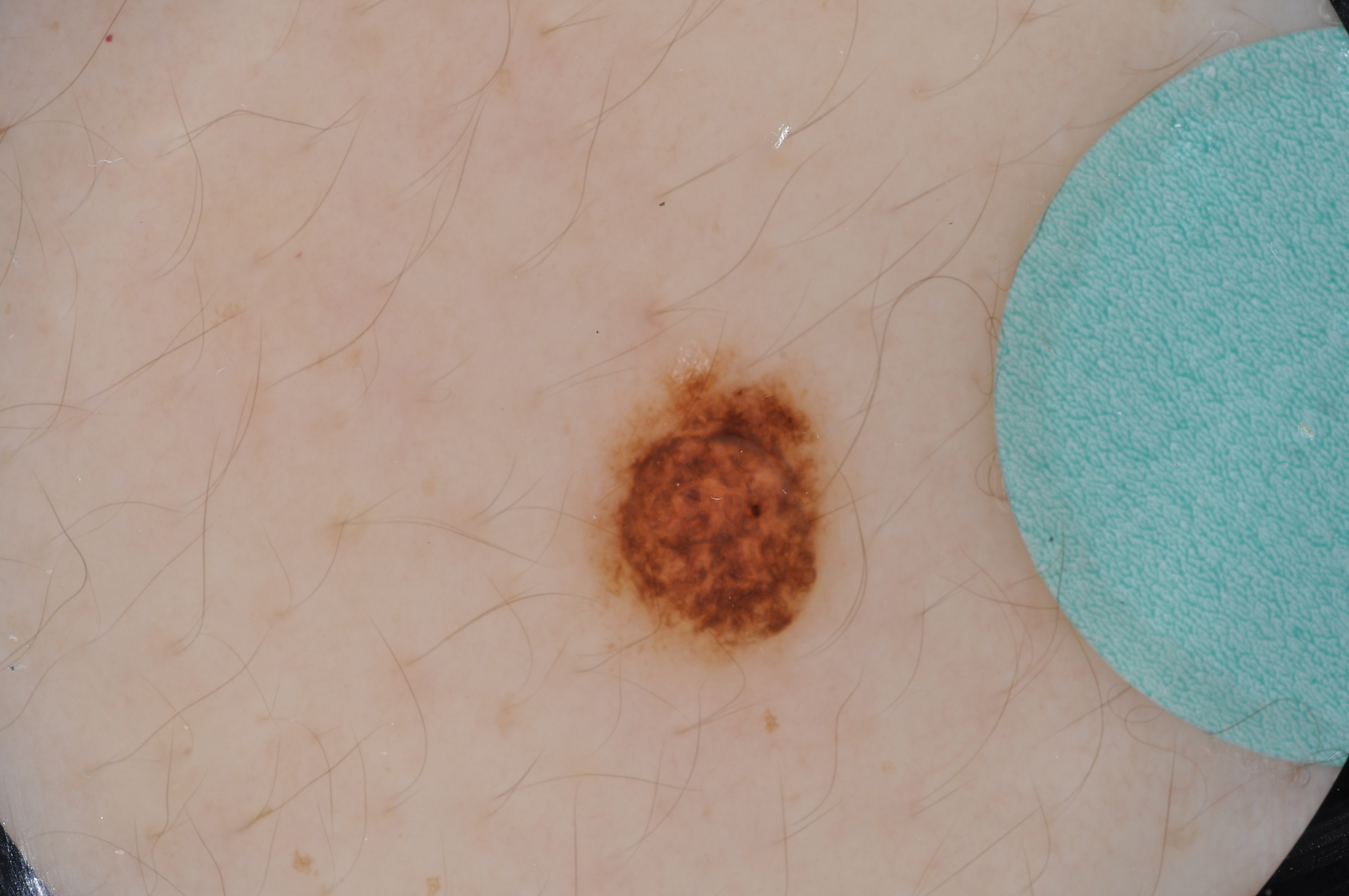Case summary:
– patient — female, aged 13 to 17
– imaging — dermoscopy of a skin lesion
– lesion bbox — bbox=[579, 344, 855, 672]
– size — ~5% of the field
– dermoscopic findings — pigment network; absent: globules, milia-like cysts, negative network, and streaks
– diagnostic label — a melanocytic nevus, a benign skin lesion